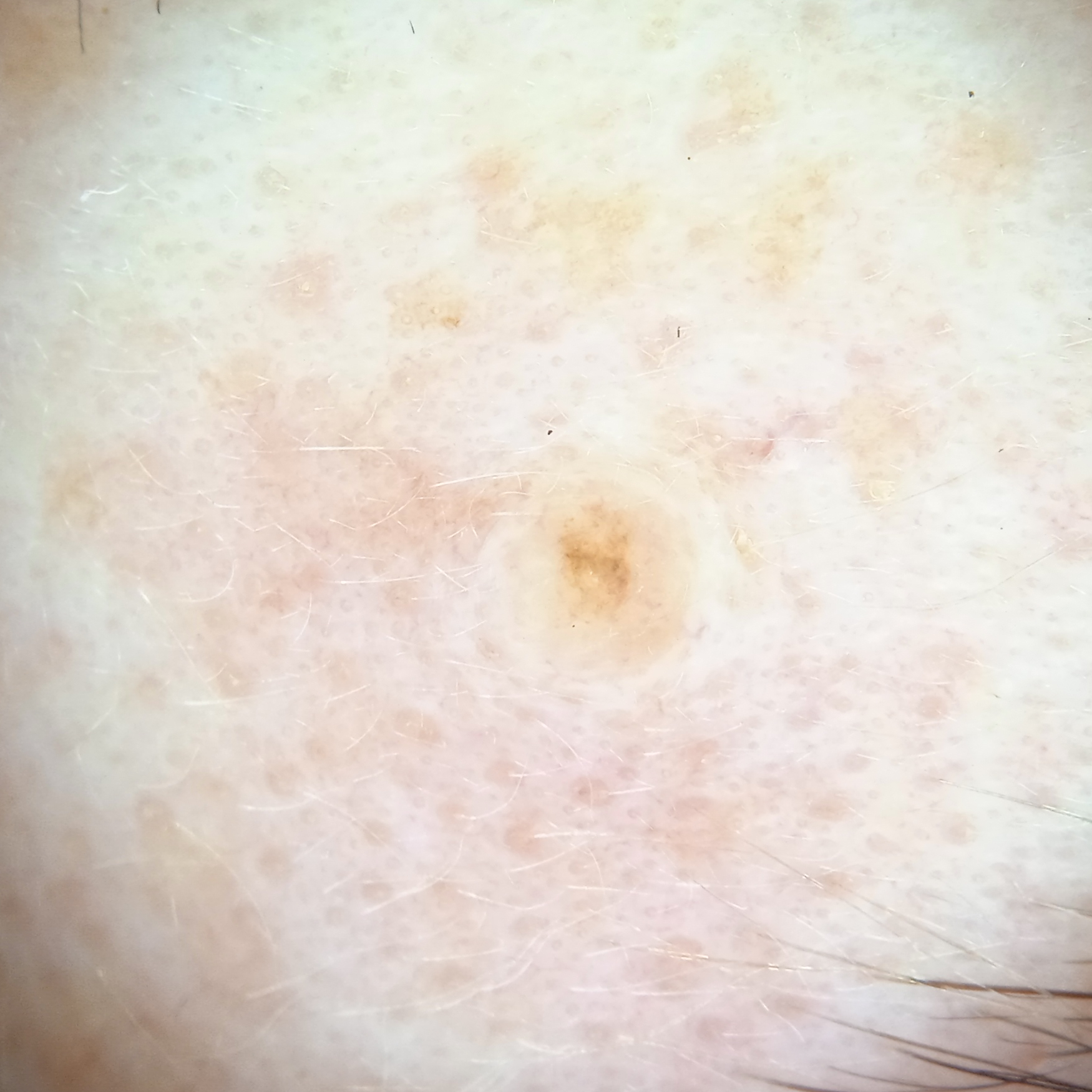Referred for assessment of suspected melanoma.
A female subject 50 years of age.
A moderate number of moles by the patient's own estimate.
A dermoscopic image of a skin lesion.
The patient says their skin reddens painfully with sun exposure.
The lesion is located on the face.
The lesion measures approximately 1.8 mm.
The lesion was assessed as a melanocytic nevus.